A dermoscopic photograph of a skin lesion:
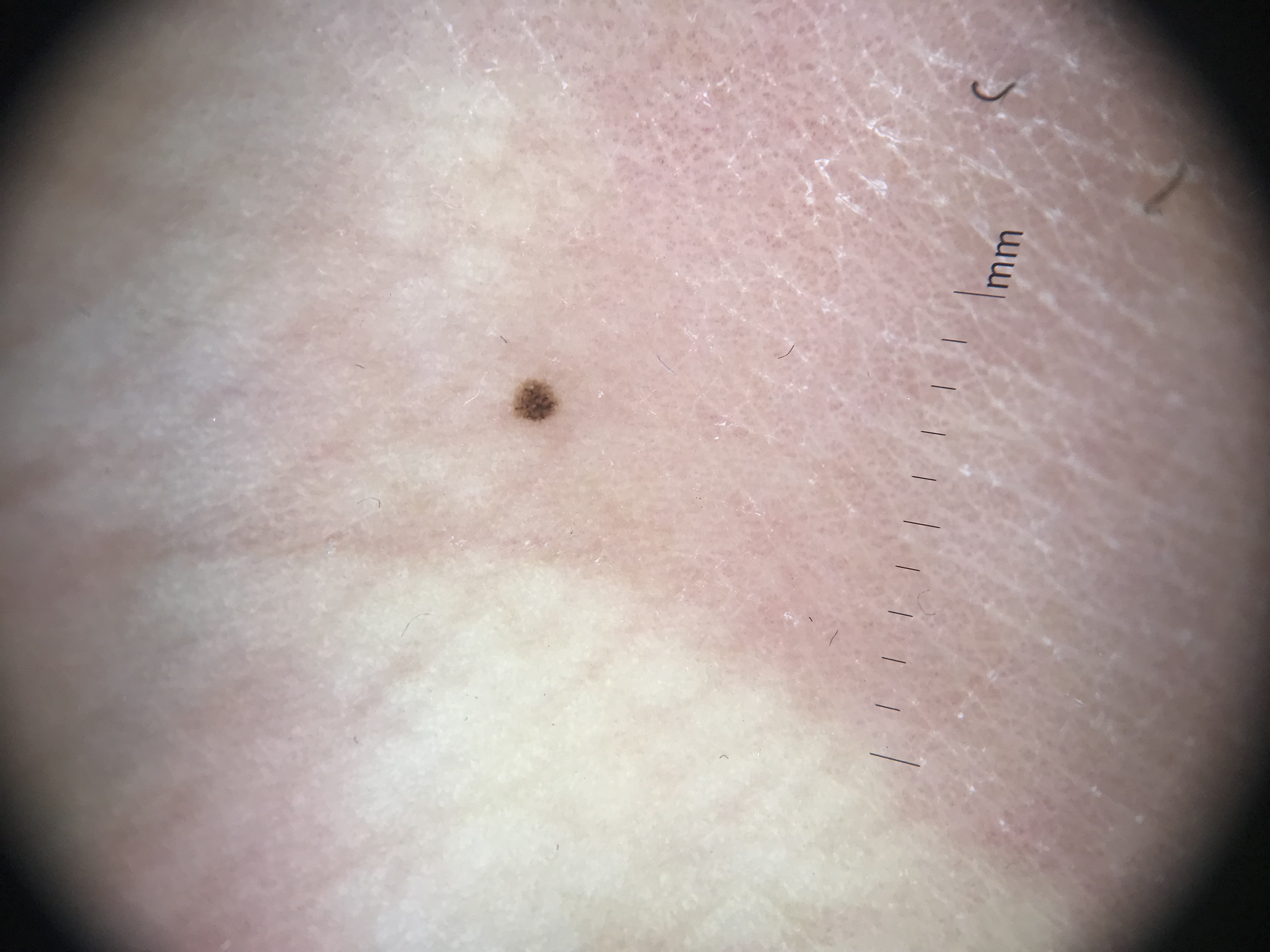Consistent with a benign lesion — an acral dysplastic junctional nevus.